The affected area is the arm, back of the hand and leg; the patient is 40–49, female; the photograph was taken at an angle.
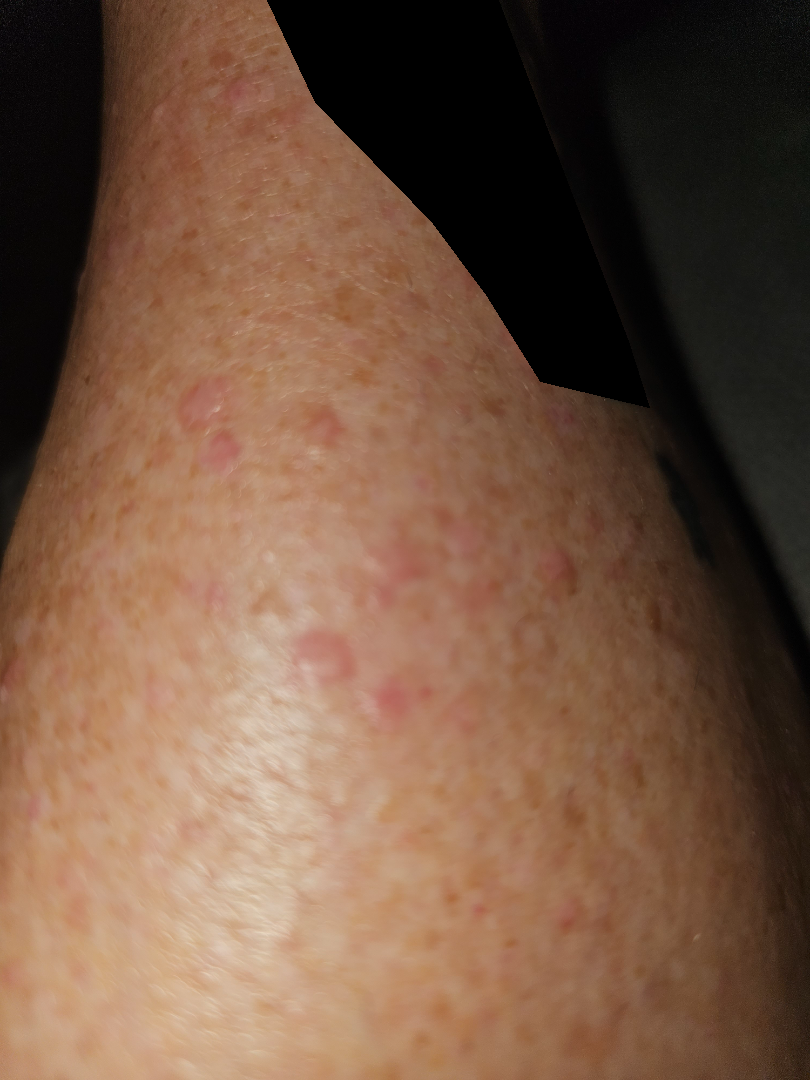Notes:
* self-categorized as — a rash
* history — less than one week
* symptoms — itching
* diagnostic considerations — the reviewer's impression was Stasis Dermatitis